Per the chart, a previous melanoma; a female subject roughly 65 years of age; a skin lesion imaged with contact-polarized dermoscopy; recorded as FST I.
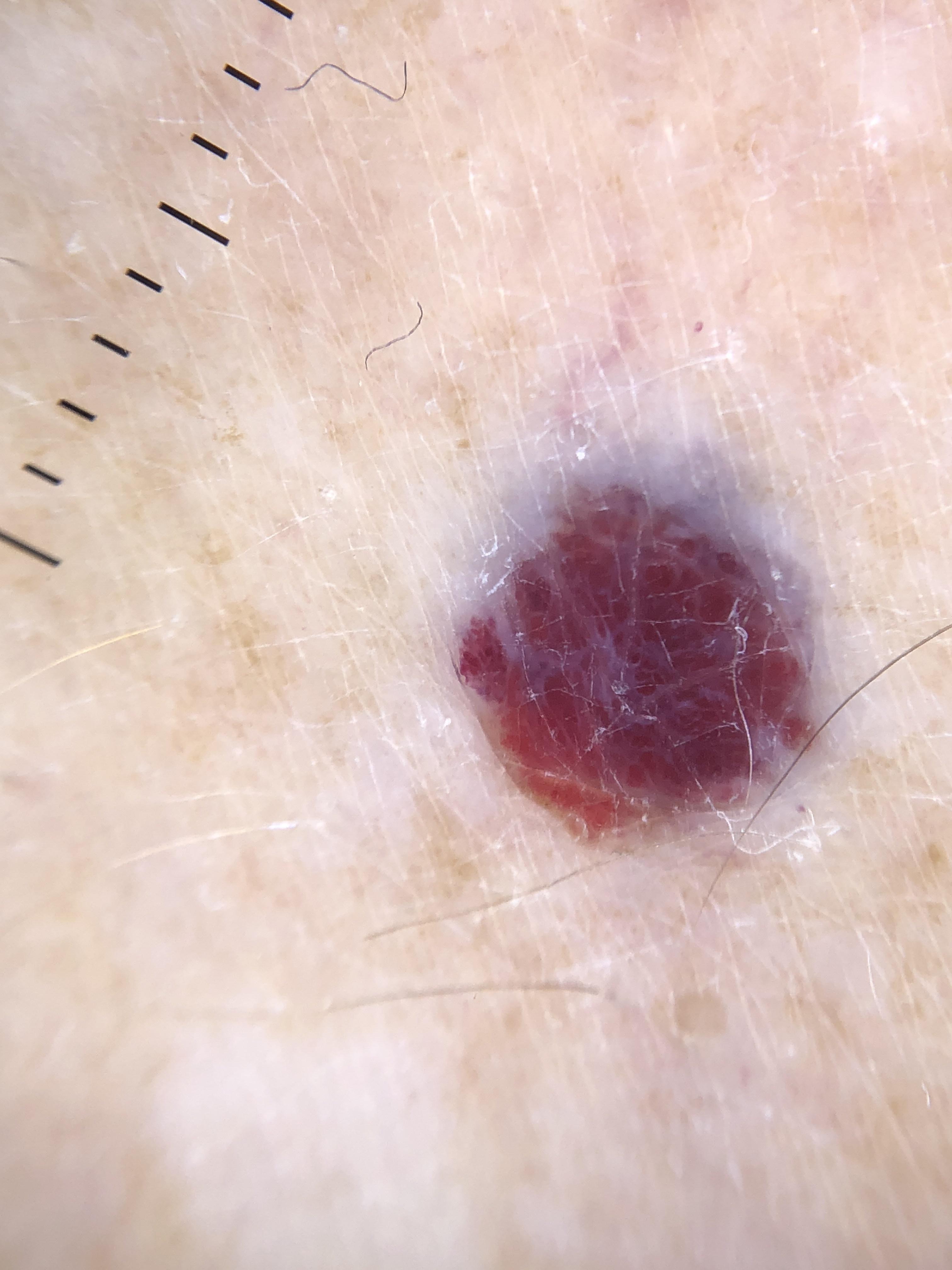The lesion is on a lower extremity. Histopathologically confirmed as a benign vascular lesion.